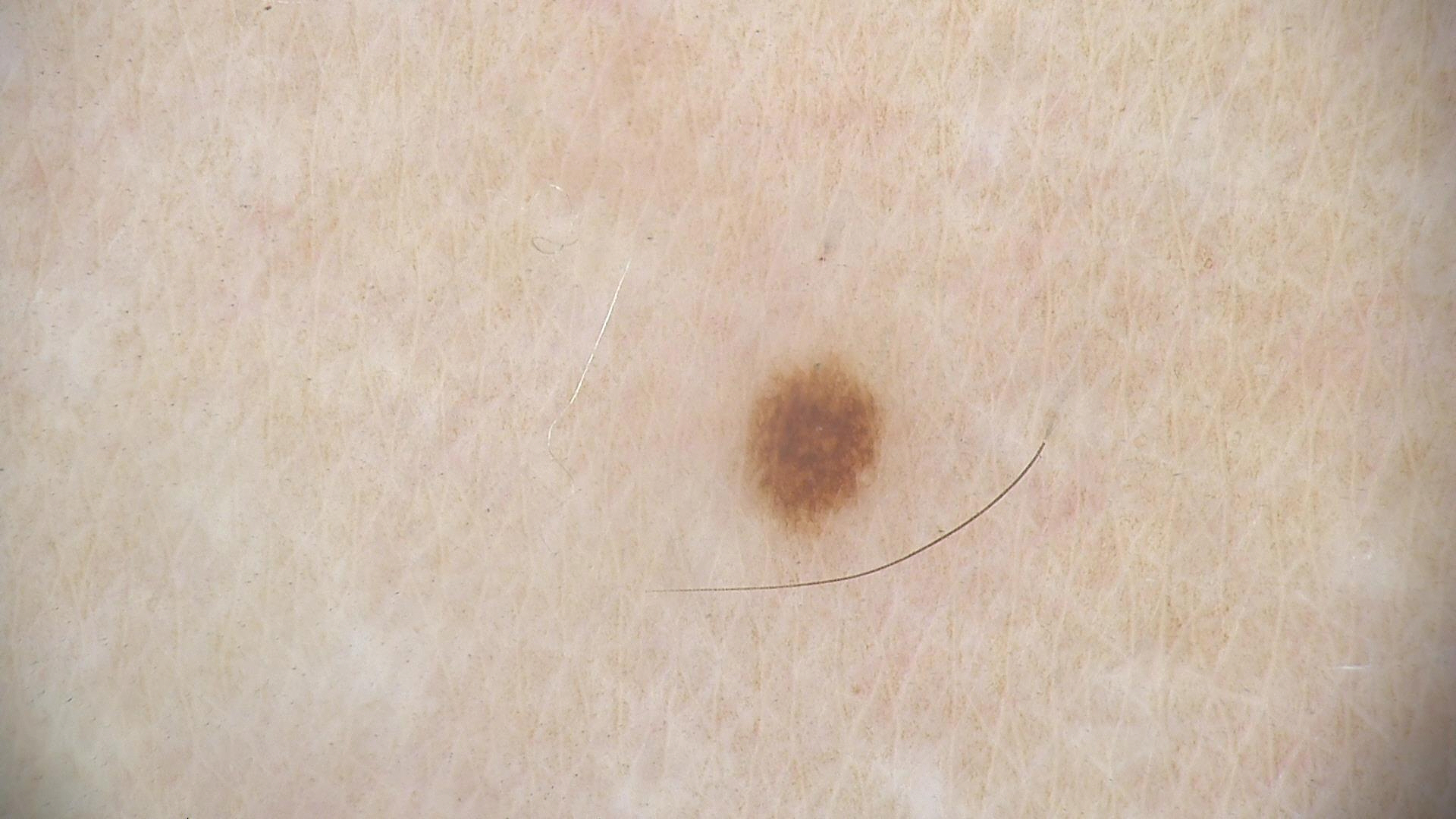Q: What is the imaging modality?
A: dermatoscopy
Q: What was the diagnostic impression?
A: dysplastic junctional nevus (expert consensus)